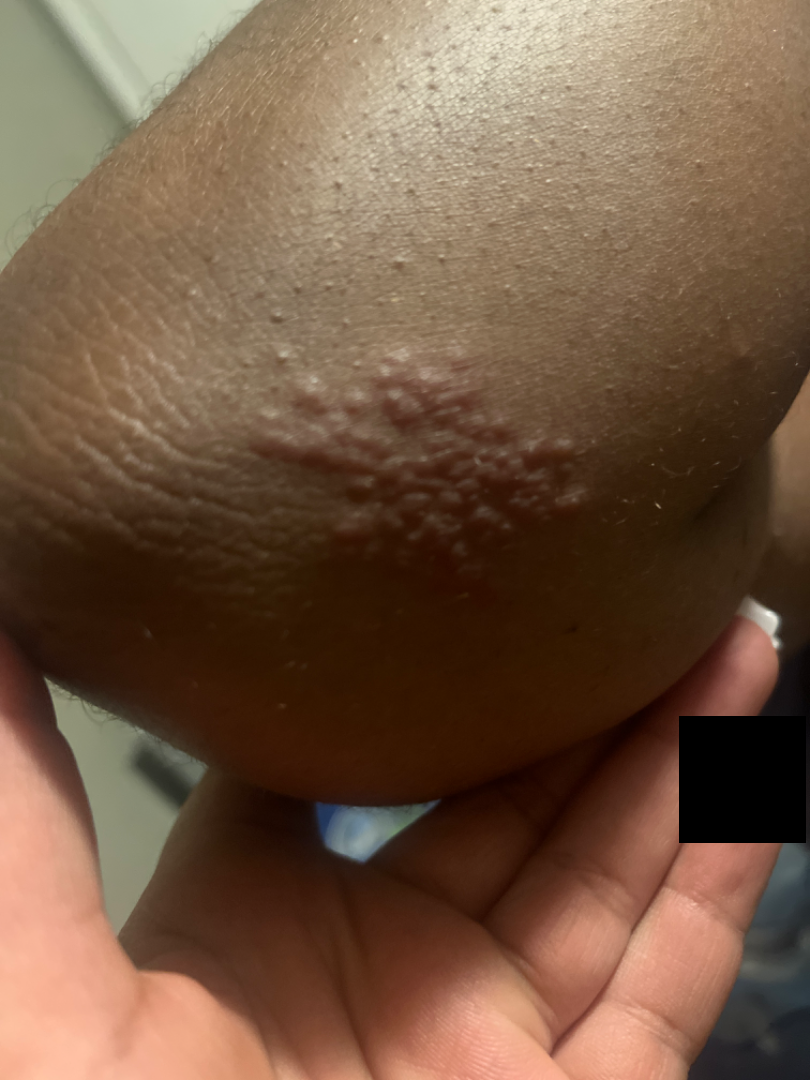Patient information: This is a close-up image. Review: A single dermatologist reviewed the case: the differential includes Herpes Zoster, Allergic Contact Dermatitis and Herpes Simplex, with no clear leading consideration.